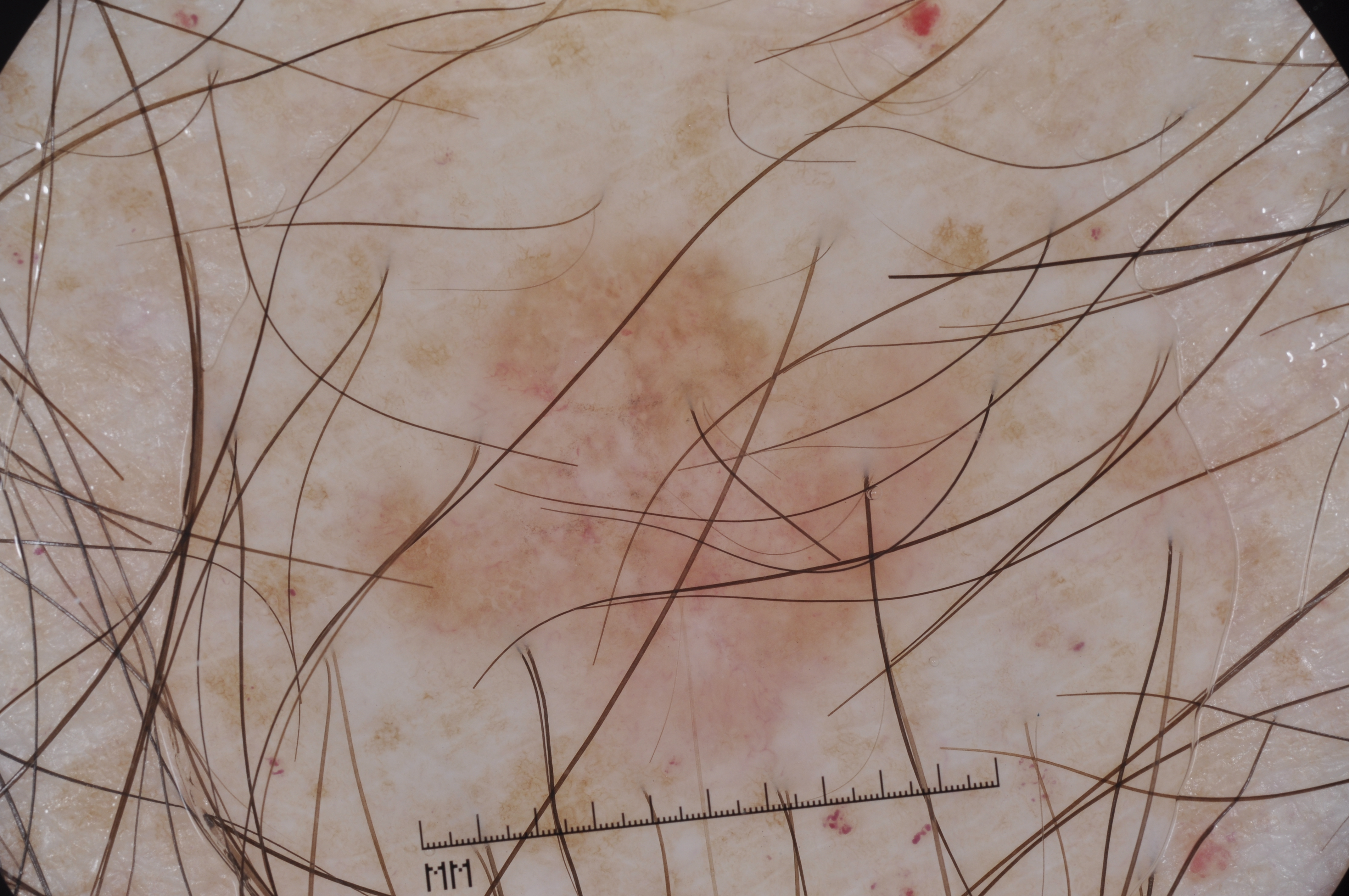Case summary:
This is a dermoscopic photograph of a skin lesion. The patient is a male aged around 65. A moderately sized lesion. In (x1, y1, x2, y2) order, the lesion spans bbox=[314, 191, 1054, 848]. The dermoscopic pattern shows negative network and pigment network; no milia-like cysts or streaks.
Conclusion:
Histopathology confirmed a melanoma.